The subject is a female approximately 60 years of age; this is a dermoscopic photograph of a skin lesion:
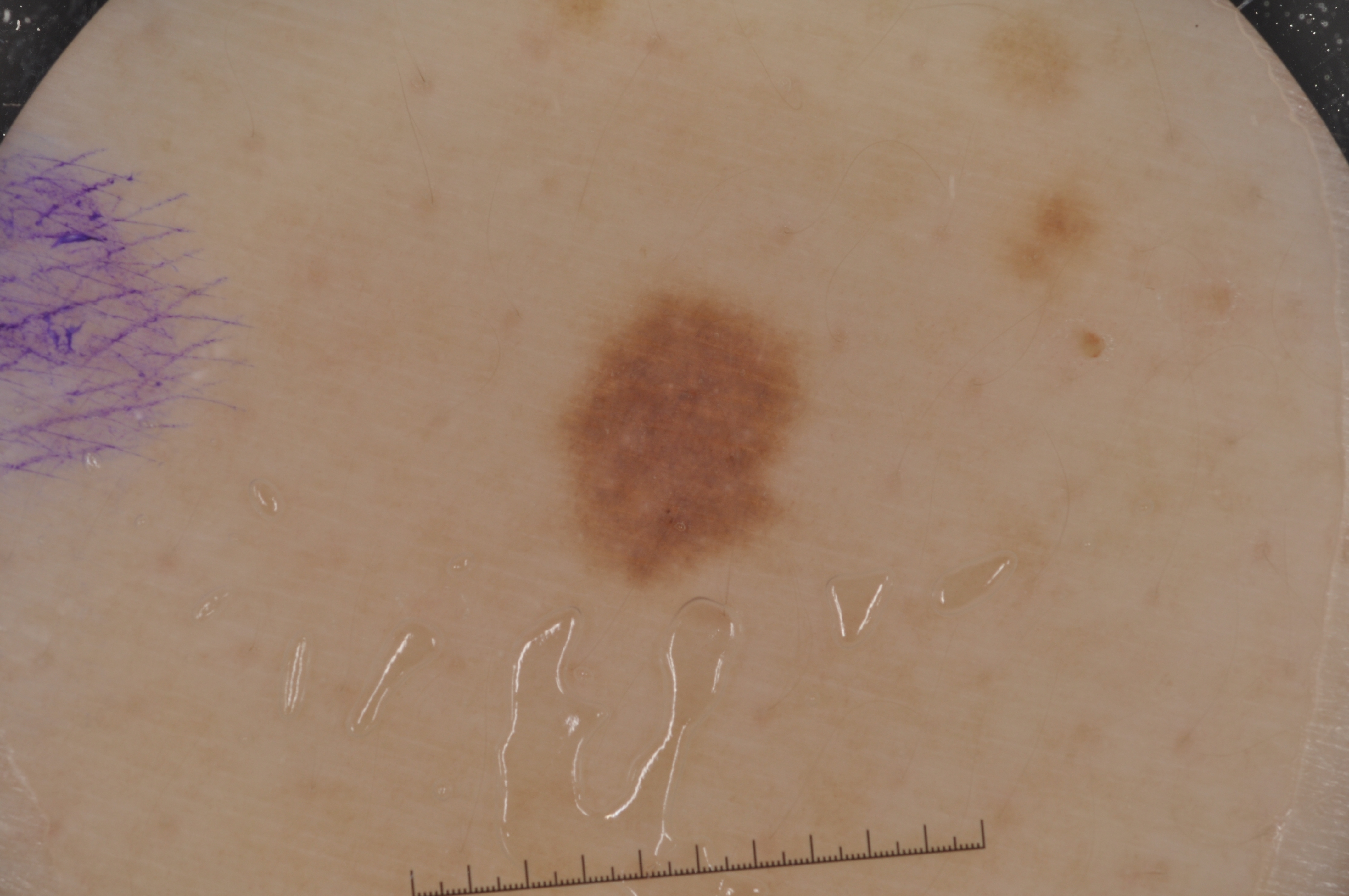size: small | location: box(559, 287, 811, 581) | absent dermoscopic findings: streaks, negative network, pigment network, and milia-like cysts | diagnosis: a melanocytic nevus, a benign lesion.